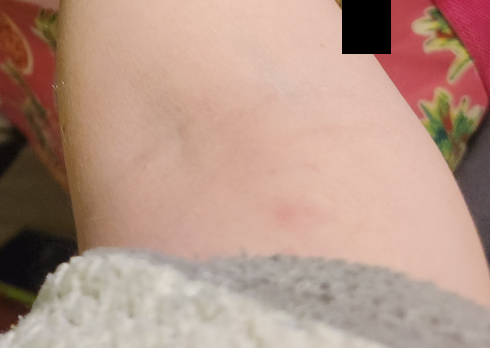Q: Texture?
A: raised or bumpy
Q: When did this start?
A: about one day
Q: Image view?
A: at a distance
Q: Who is the patient?
A: female
Q: How does the patient describe it?
A: a rash
Q: What is the patient's skin tone?
A: Fitzpatrick skin type IV; non-clinician graders estimated 3 on the Monk skin tone scale
Q: Where on the body?
A: arm
Q: Reported symptoms?
A: itching, burning and pain
Q: What conditions are considered?
A: most consistent with Eczema